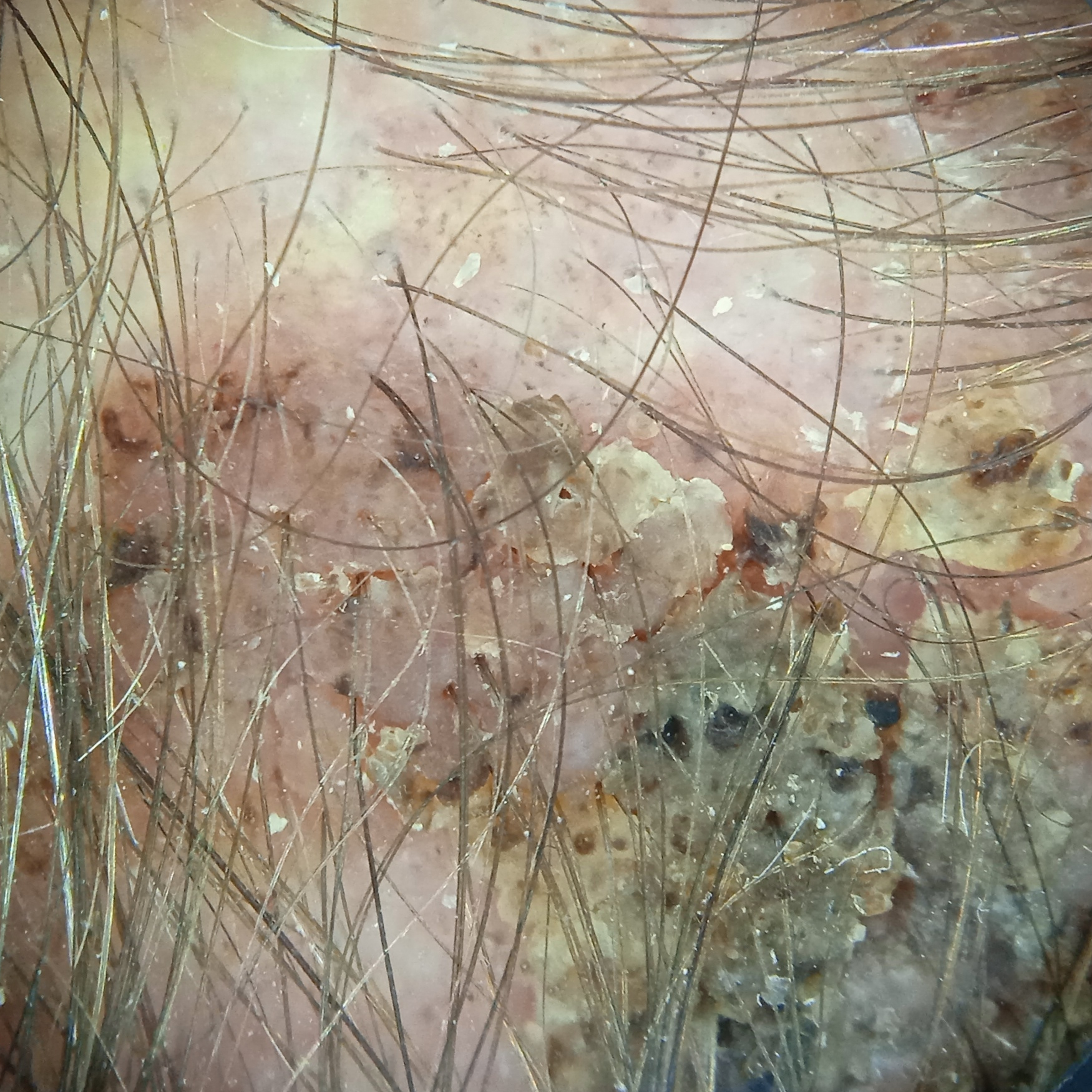A male patient age 72. Acquired for a research image collection, with no referral diagnosis. The patient says their skin tans without first burning. The patient describes having a moderate number of moles. Located on the head. The lesion is about 19.2 mm across. The diagnostic impression was a seborrheic keratosis.